The photograph is a close-up of the affected area:
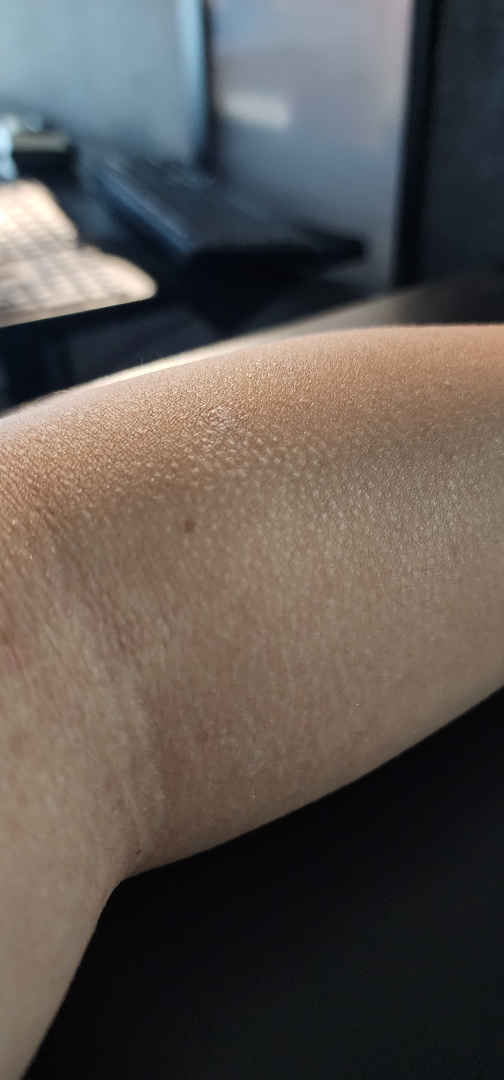Findings:
– assessment: indeterminate